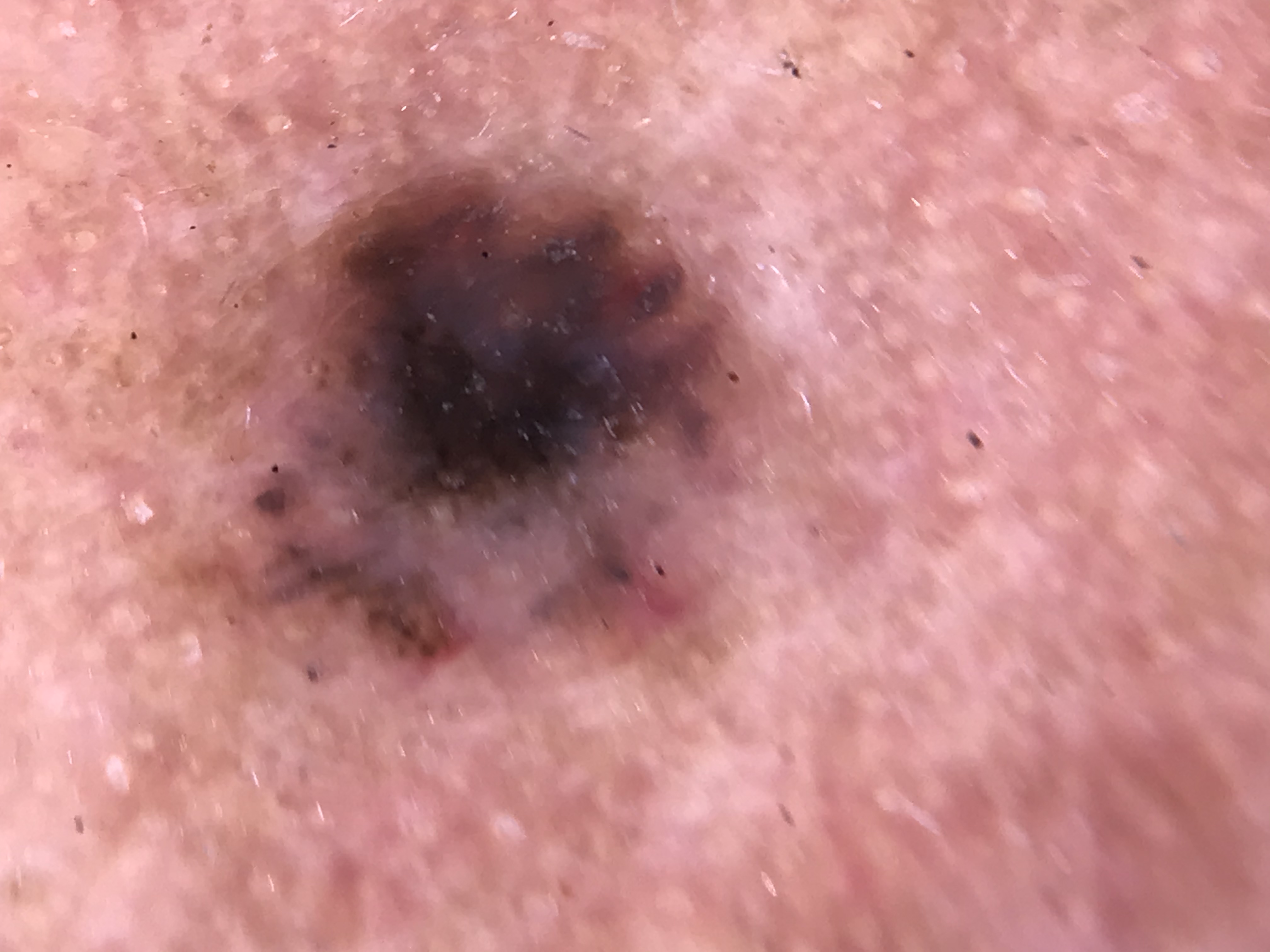Case: Dermoscopy of a skin lesion. This is a keratinocytic lesion. Pathology: The biopsy diagnosis was a basal cell carcinoma.